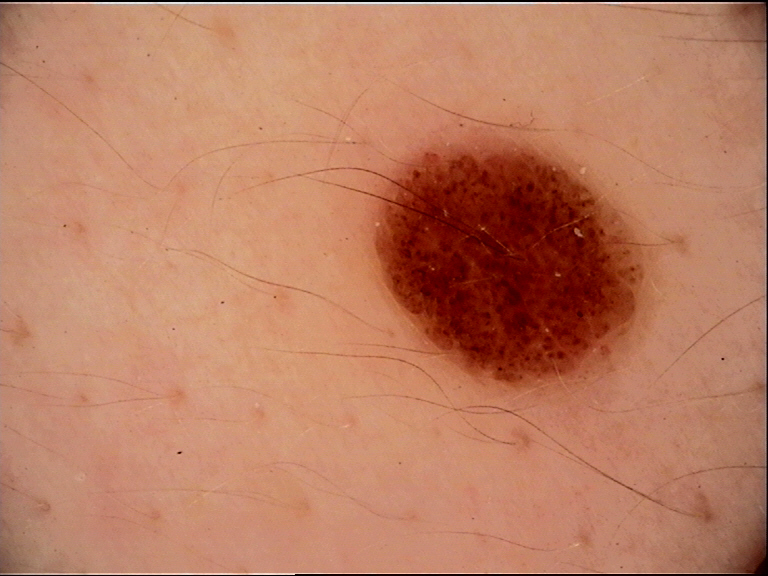Summary:
A dermoscopic image of a skin lesion.
Conclusion:
The diagnosis was a banal lesion — a compound nevus.